The photo was captured at an angle — 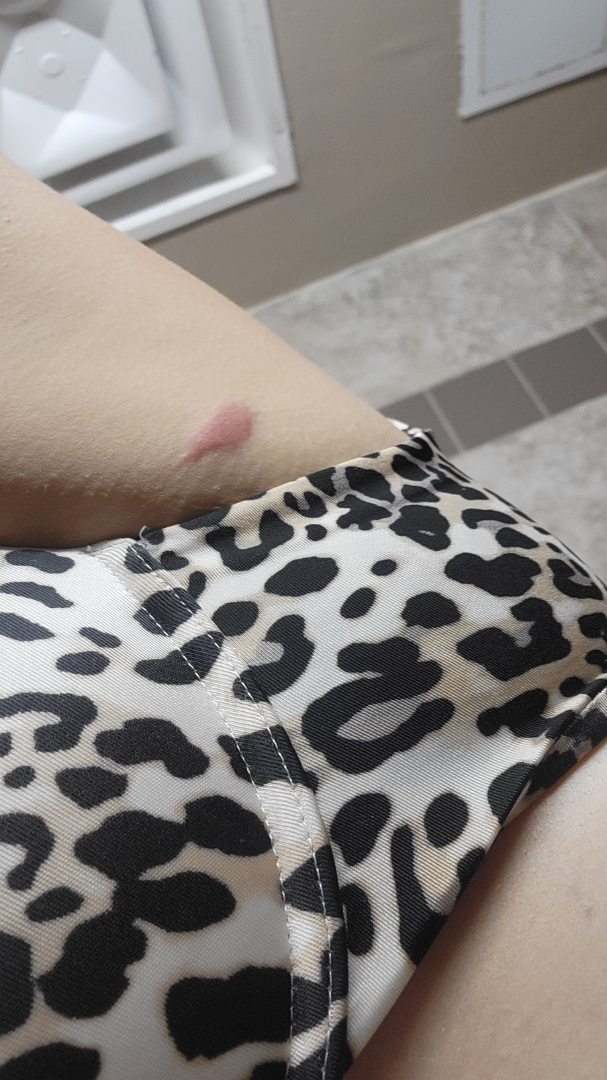<summary>
<assessment>indeterminate from the photograph</assessment>
<systemic_symptoms>shortness of breath, joint pain, fatigue</systemic_symptoms>
<symptoms>itching, burning</symptoms>
<texture>raised or bumpy</texture>
<duration>less than one week</duration>
</summary>